A dermoscopic photograph of a skin lesion.
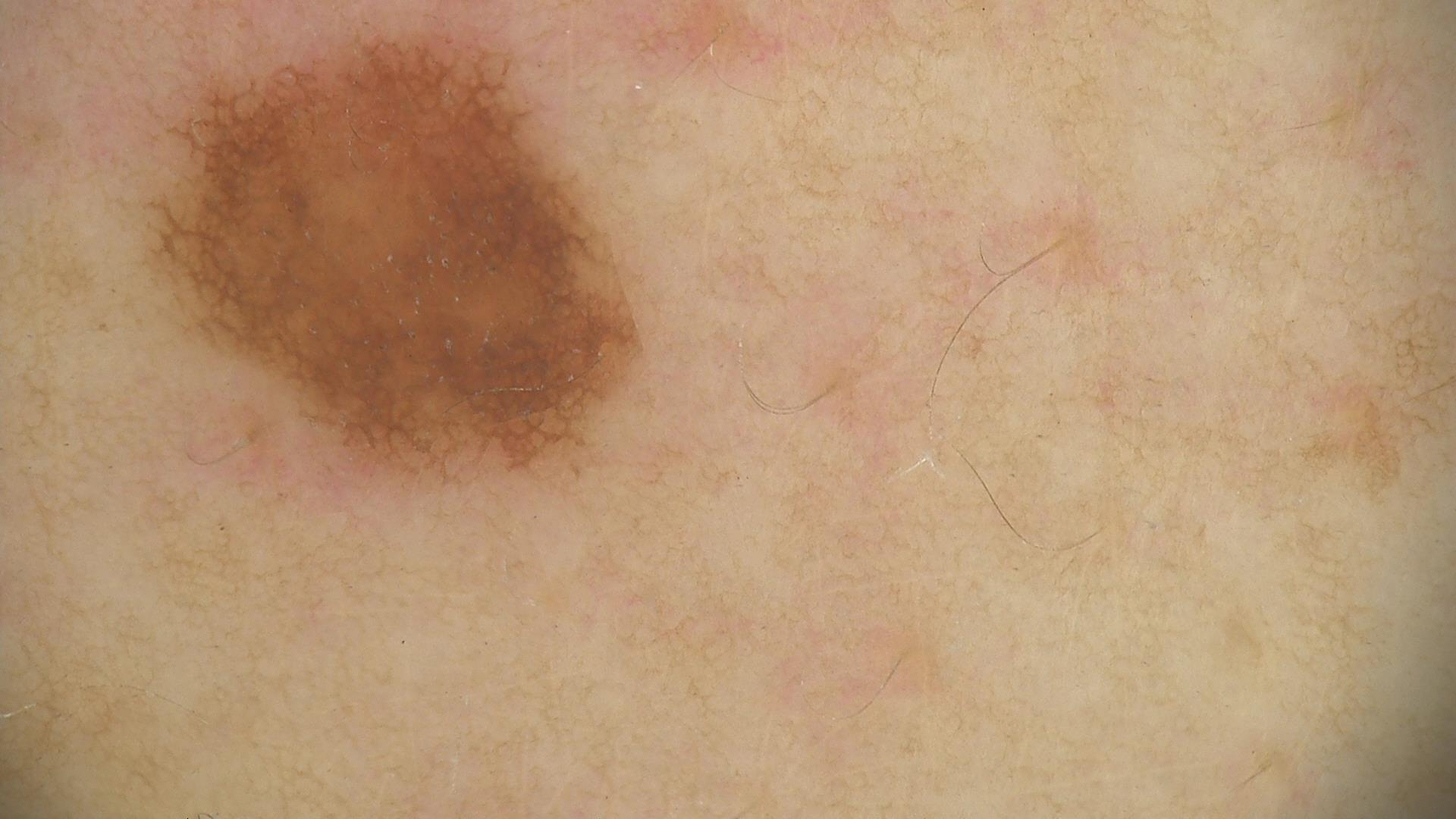| feature | finding |
|---|---|
| label | dysplastic junctional nevus (expert consensus) |